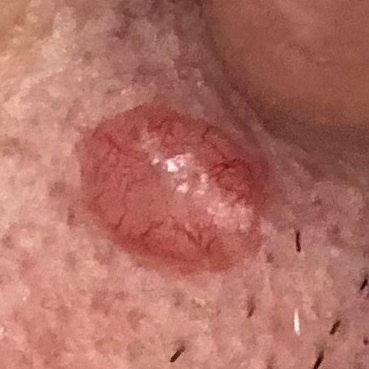History notes prior malignancy (patient or family) and pesticide exposure. A male patient in their 40s. Fitzpatrick II. The lesion is on the face. Measuring about 6 × 5 mm. Histopathological examination showed a basal cell carcinoma.